A dermoscopy image of a single skin lesion.
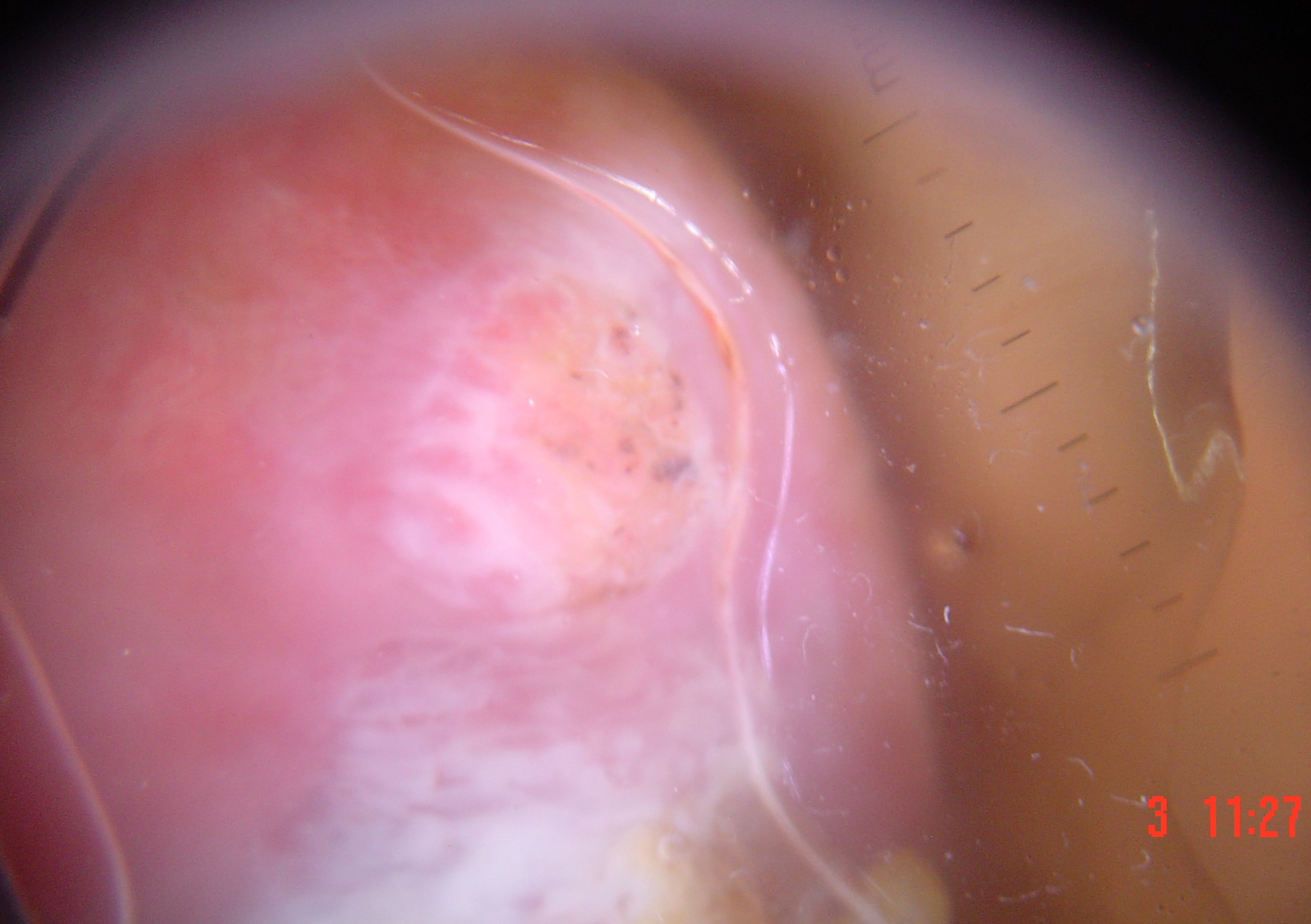Conclusion:
Histopathology confirmed a keratinocytic, malignant lesion — a squamous cell carcinoma.